Self-categorized by the patient as skin that appeared healthy to them. This image was taken at a distance. The front of the torso is involved. The subject is female. Symptoms reported: itching and bothersome appearance. Texture is reported as raised or bumpy. The contributor notes the condition has been present for less than one week.
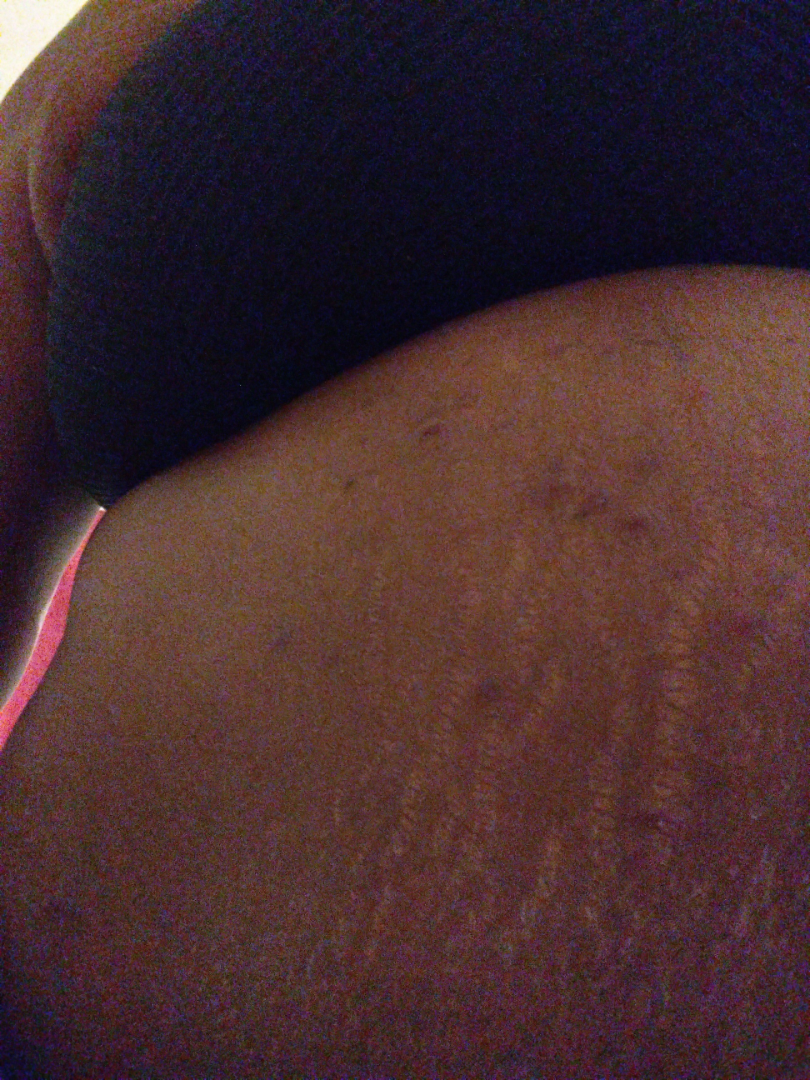Three independent reviewers: the differential includes Scabies and Pruritic urticarial papules and plaques of pregnancy, with no clear leading consideration.